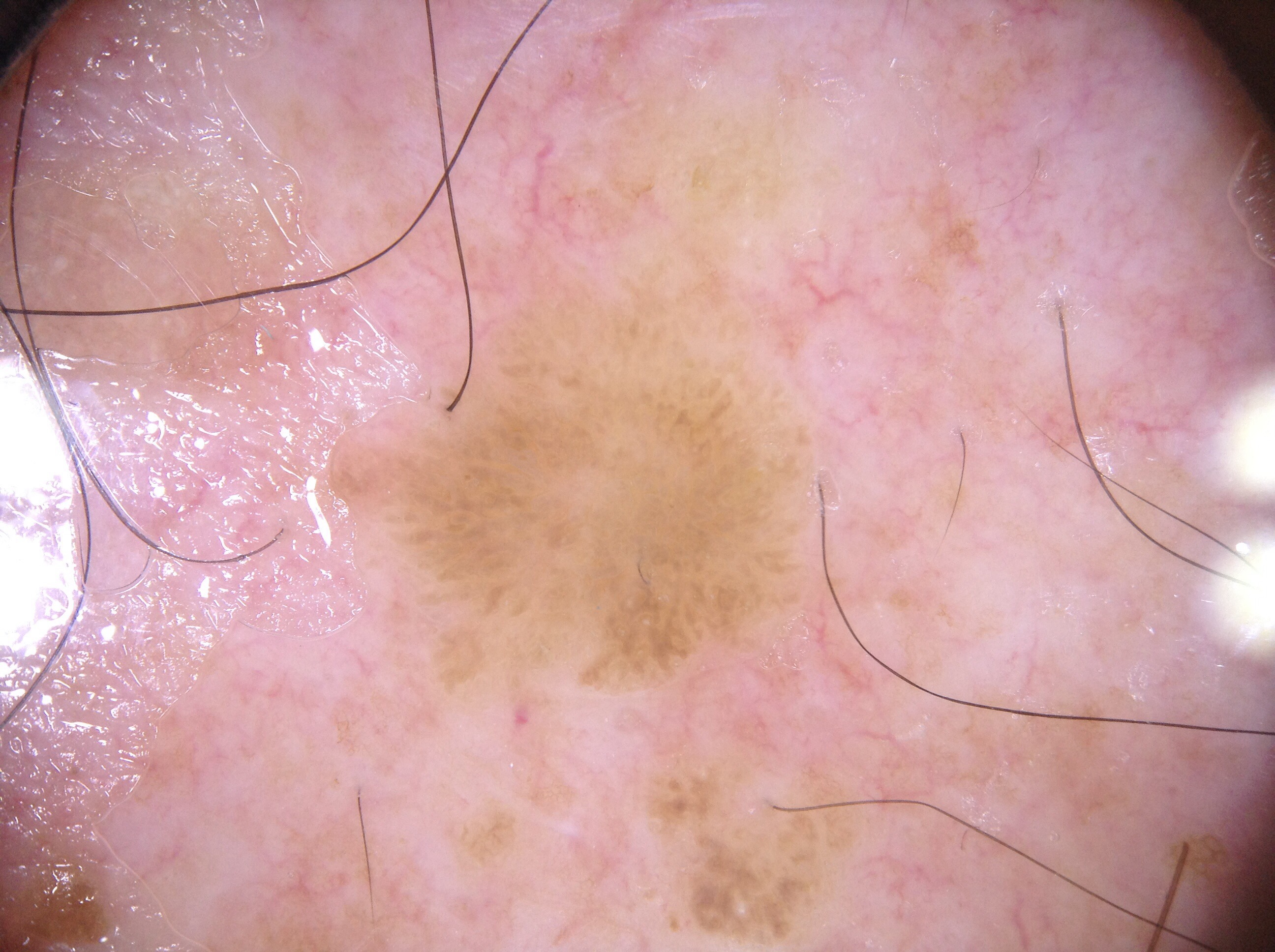modality = dermoscopic image; lesion bbox = [359,394,777,669]; dermoscopic features assessed but absent = negative network, milia-like cysts, pigment network, and streaks; diagnosis = a seborrheic keratosis, a non-melanocytic (keratinocytic) lesion.